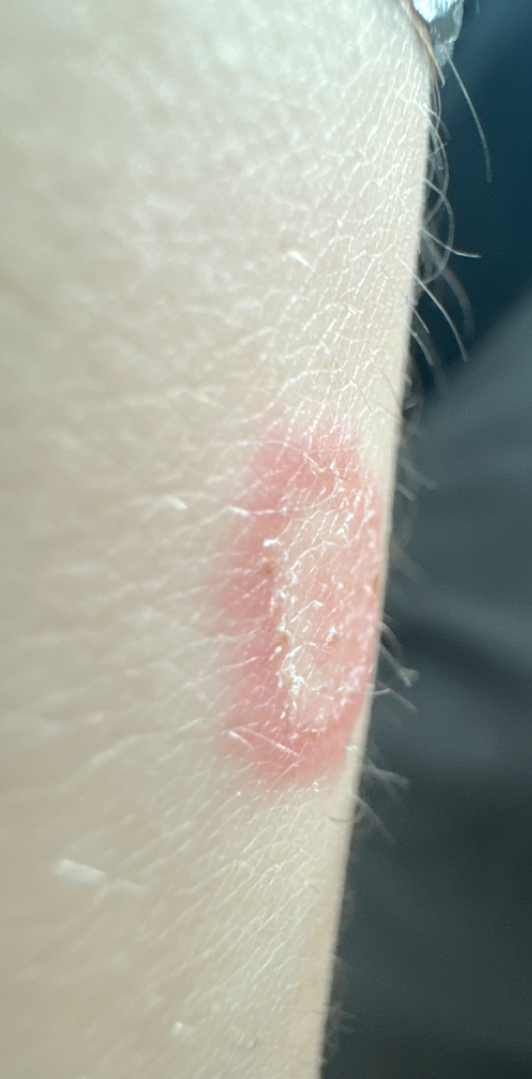The patient reported no systemic symptoms. The patient considered this a rash. Male contributor, age 18–29. The patient reports the condition has been present for one to four weeks. Texture is reported as rough or flaky. The photo was captured at an angle. The affected area is the palm and arm. The differential includes Tinea and Eczema, with no clear leading consideration; less probable is Psoriasis.